A clinical photograph of a skin lesion · the patient is Fitzpatrick skin type II:
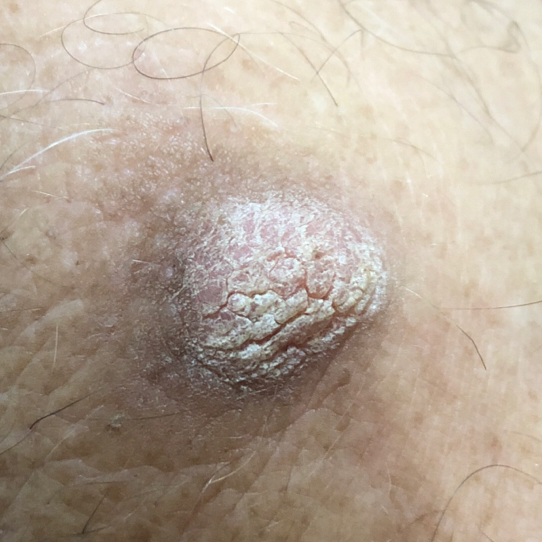The lesion is on a forearm.
Measuring about 14 × 12 mm.
Per patient report, the lesion is elevated.
Histopathologically confirmed as a premalignant lesion — an actinic keratosis.